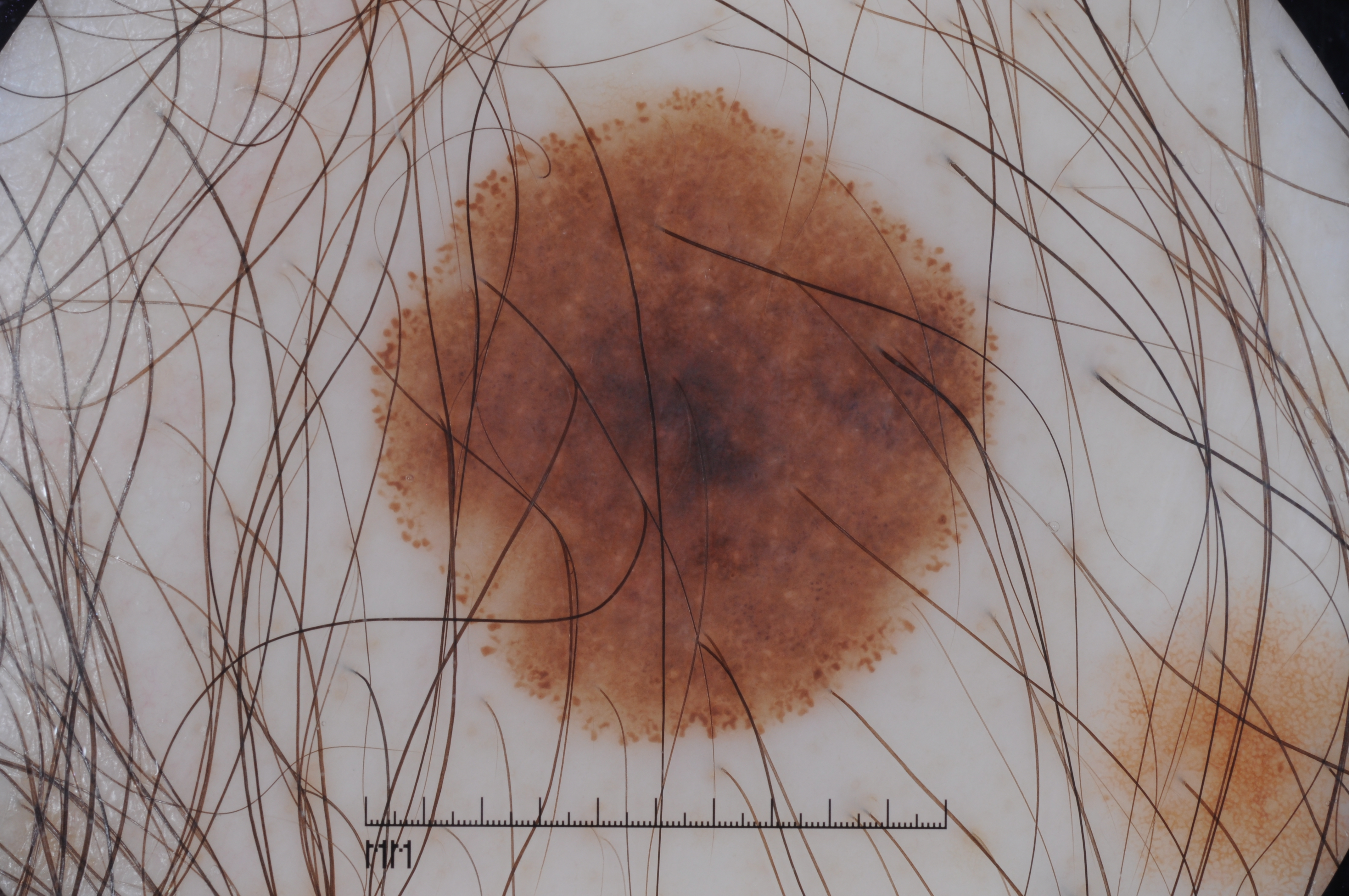A male patient, aged around 35. A dermatoscopic image of a skin lesion. The lesion takes up about 27% of the image. Dermoscopically, the lesion shows no milia-like cysts, streaks, negative network, or pigment network. As (left, top, right, bottom), the lesion is located at 363, 76, 1014, 762. Consistent with a melanocytic nevus.